A dermatoscopic image of a skin lesion.
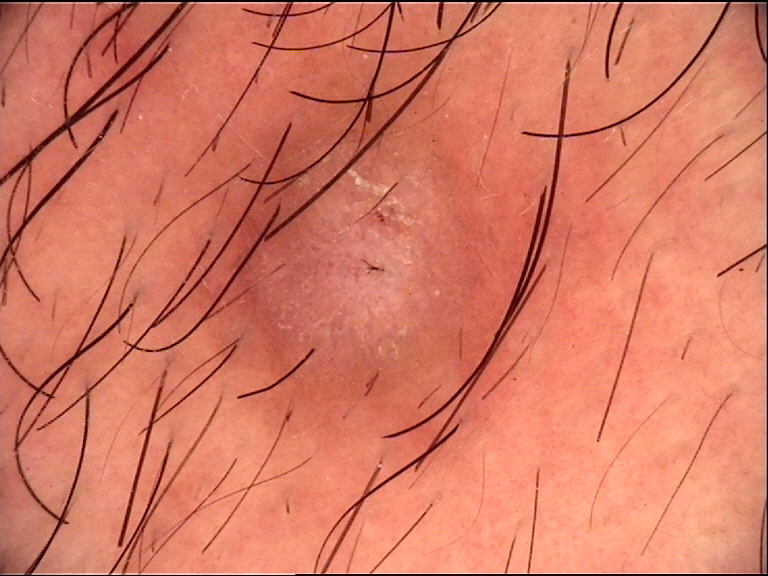Summary: The morphology is that of a fibro-histiocytic lesion. Conclusion: Labeled as a dermatofibroma.